The photo was captured at a distance — 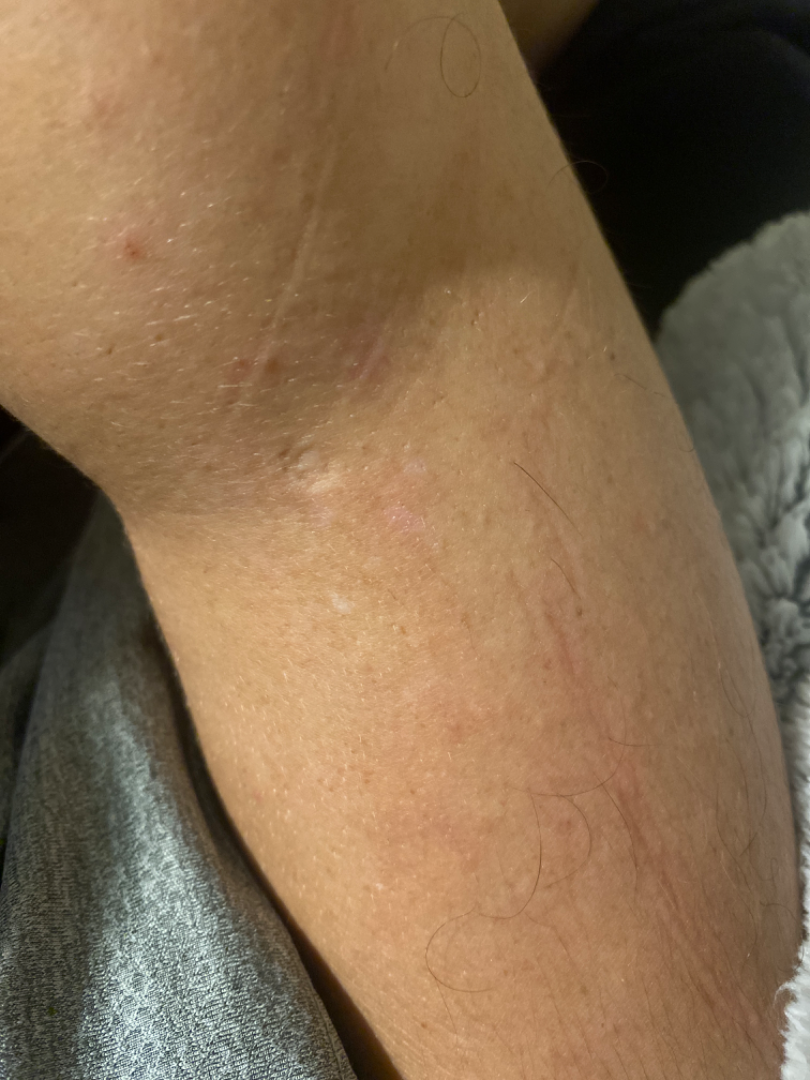diagnostic considerations — the impression on review was Eczema